The photograph is a close-up of the affected area: 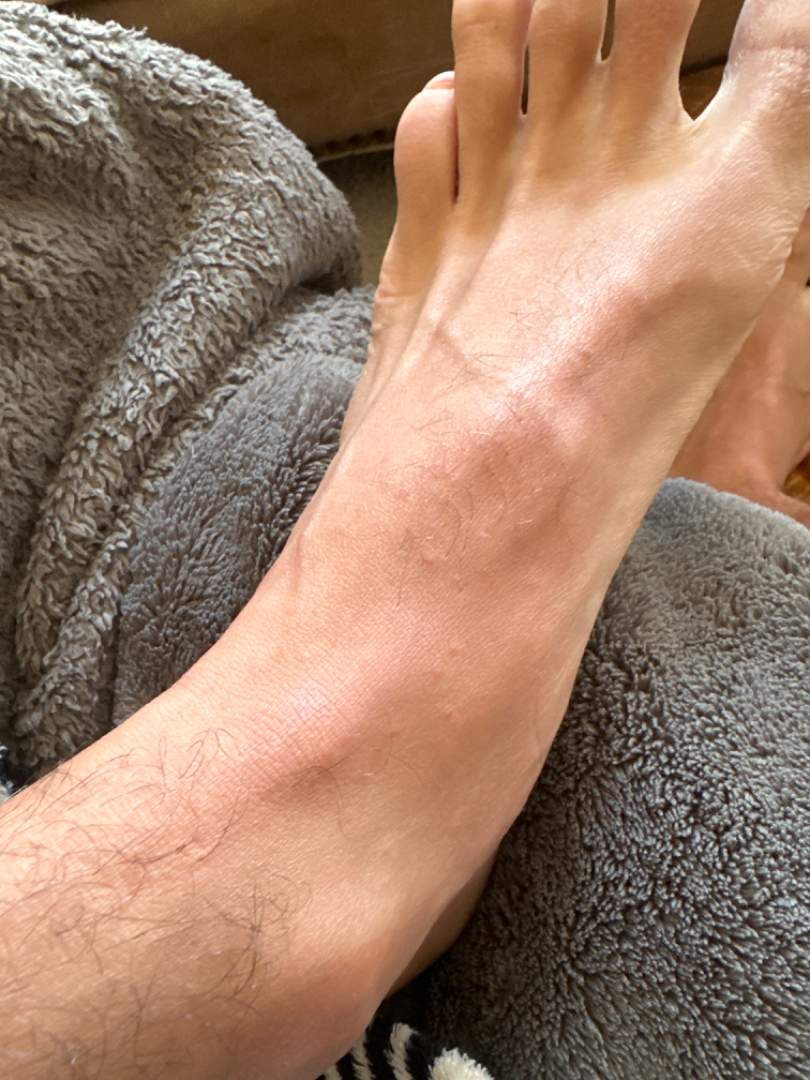assessment=could not be assessed.